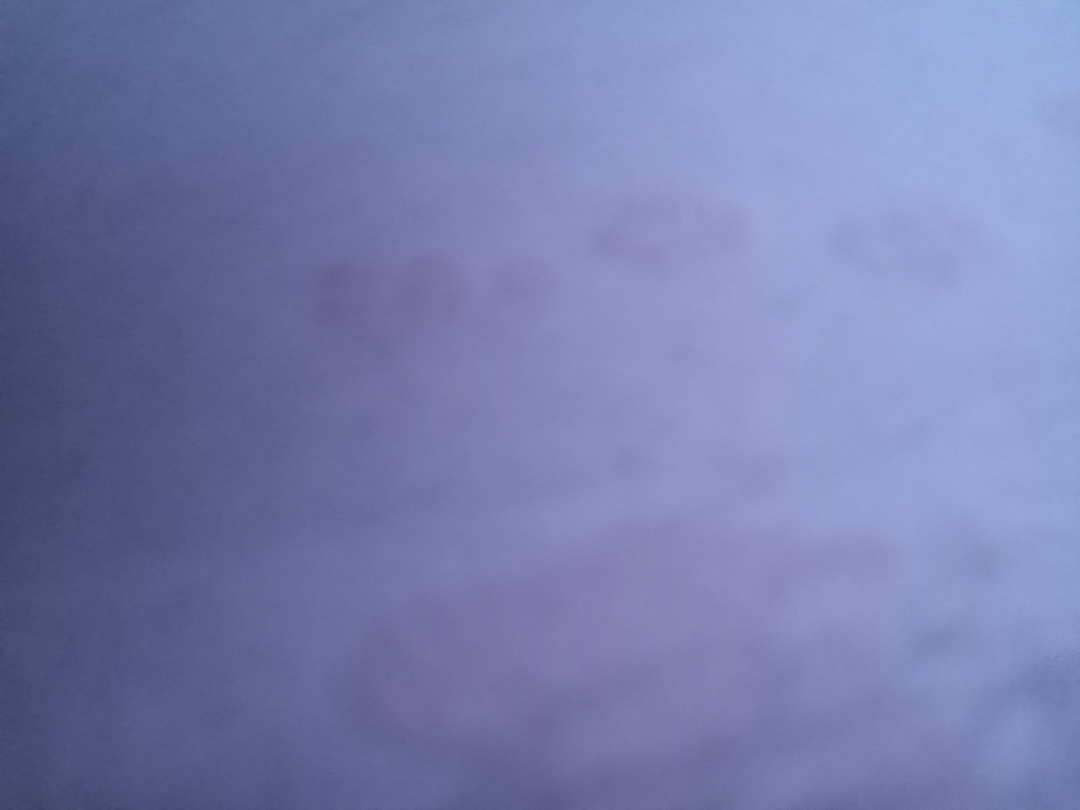Q: Could the case be diagnosed?
A: unable to determine
Q: Image view?
A: at an angle